A dermatoscopic image of a skin lesion:
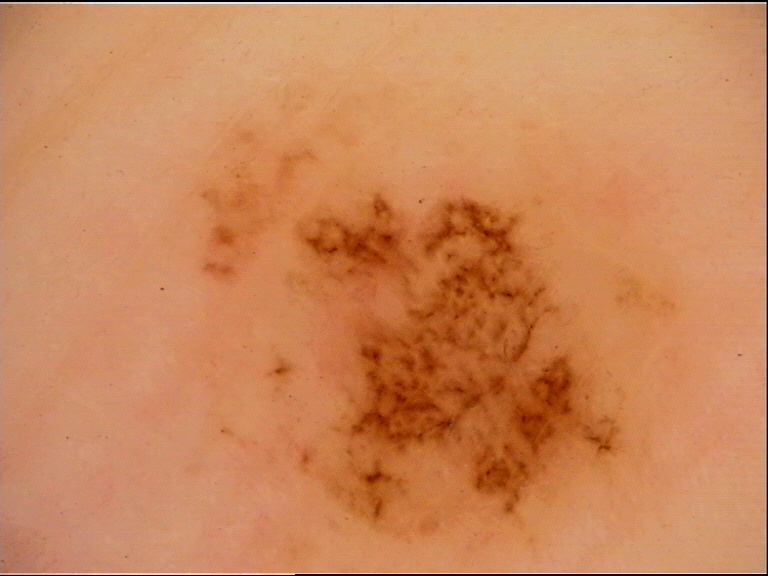The diagnostic label was a banal lesion — a dermal nevus.